A dermoscopic image of a skin lesion.
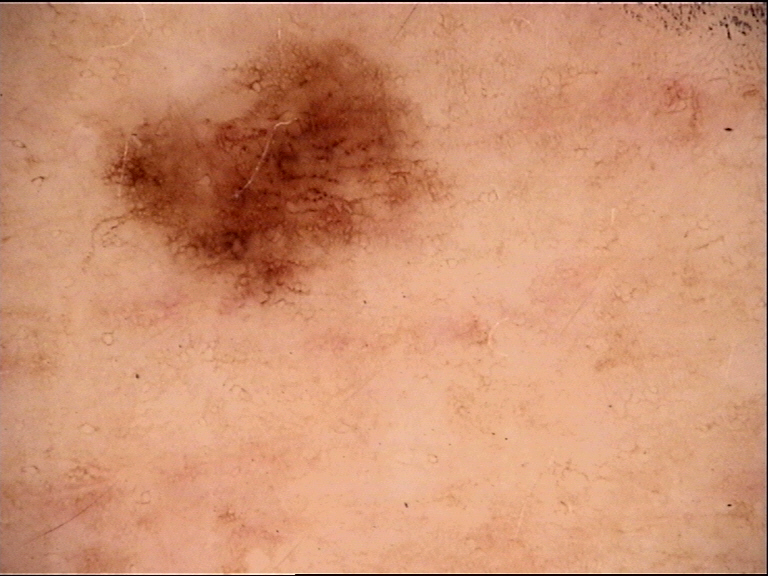{"diagnosis": {"name": "dysplastic junctional nevus", "code": "jd", "malignancy": "benign", "super_class": "melanocytic", "confirmation": "expert consensus"}}